A dermatoscopic image of a skin lesion.
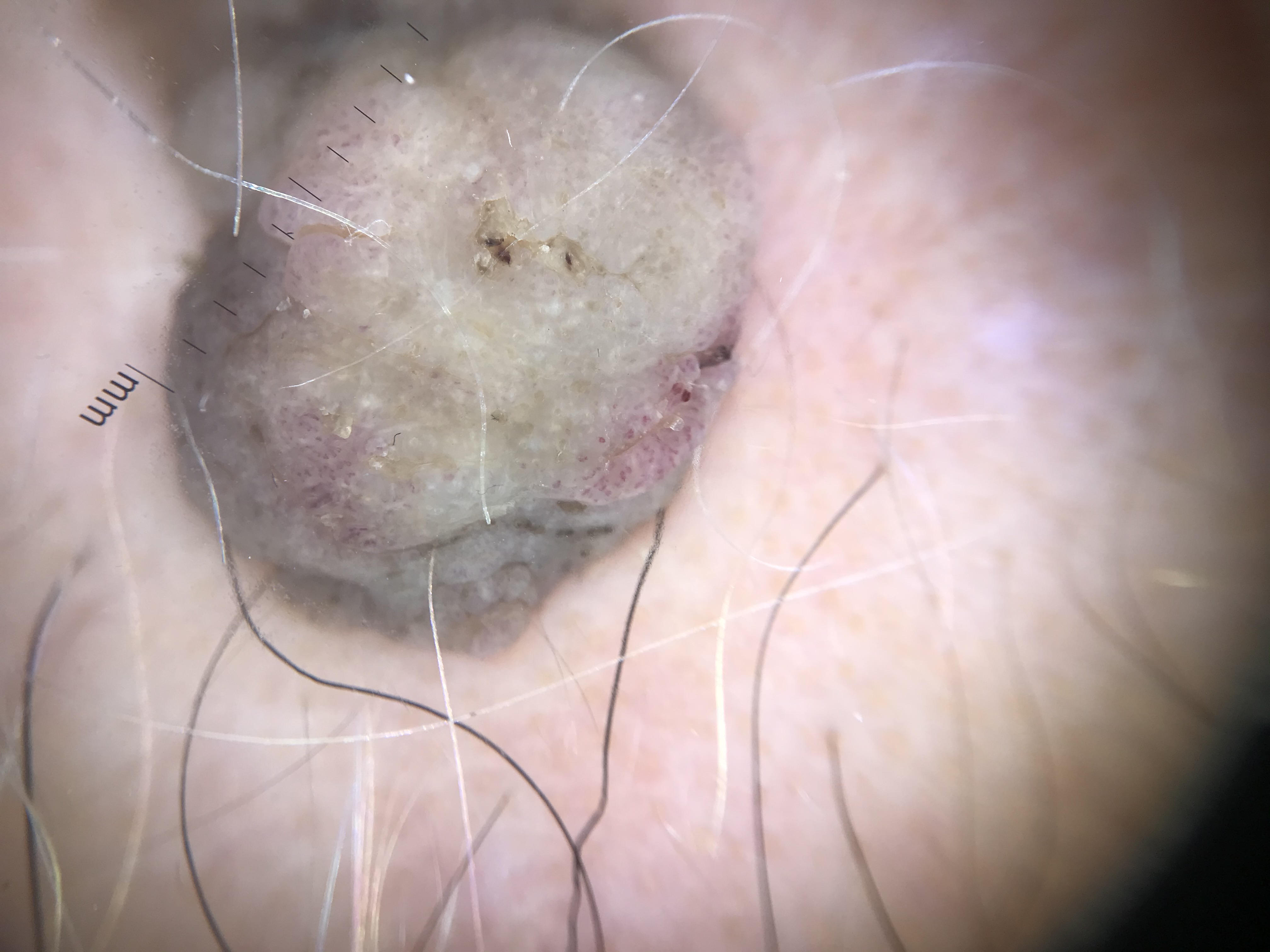The morphology is that of a keratinocytic lesion.
Diagnosed as a benign lesion — a seborrheic keratosis.